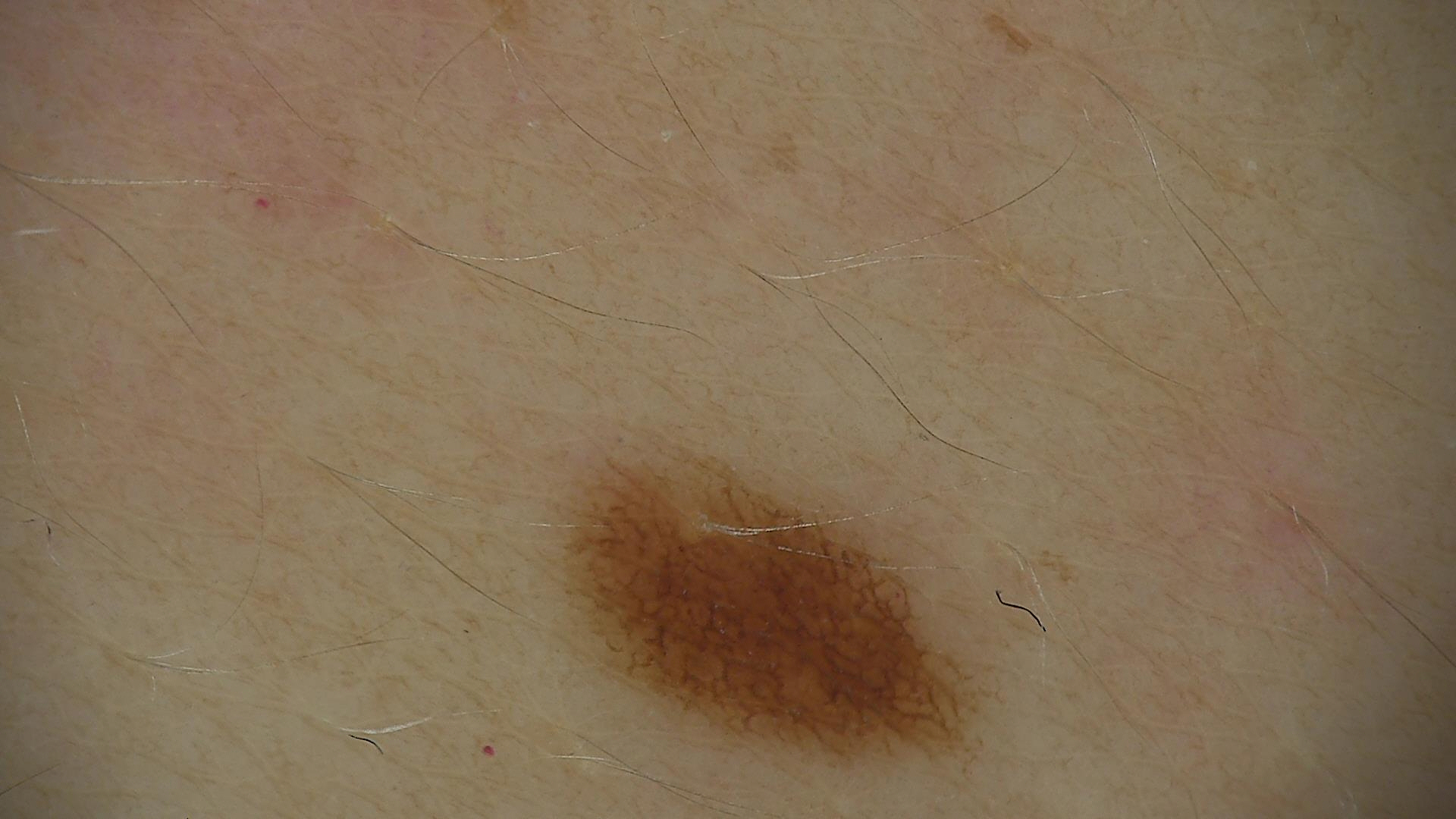Conclusion: Labeled as a dysplastic junctional nevus.